A female subject, aged around 80 · a dermatoscopic image of a skin lesion: 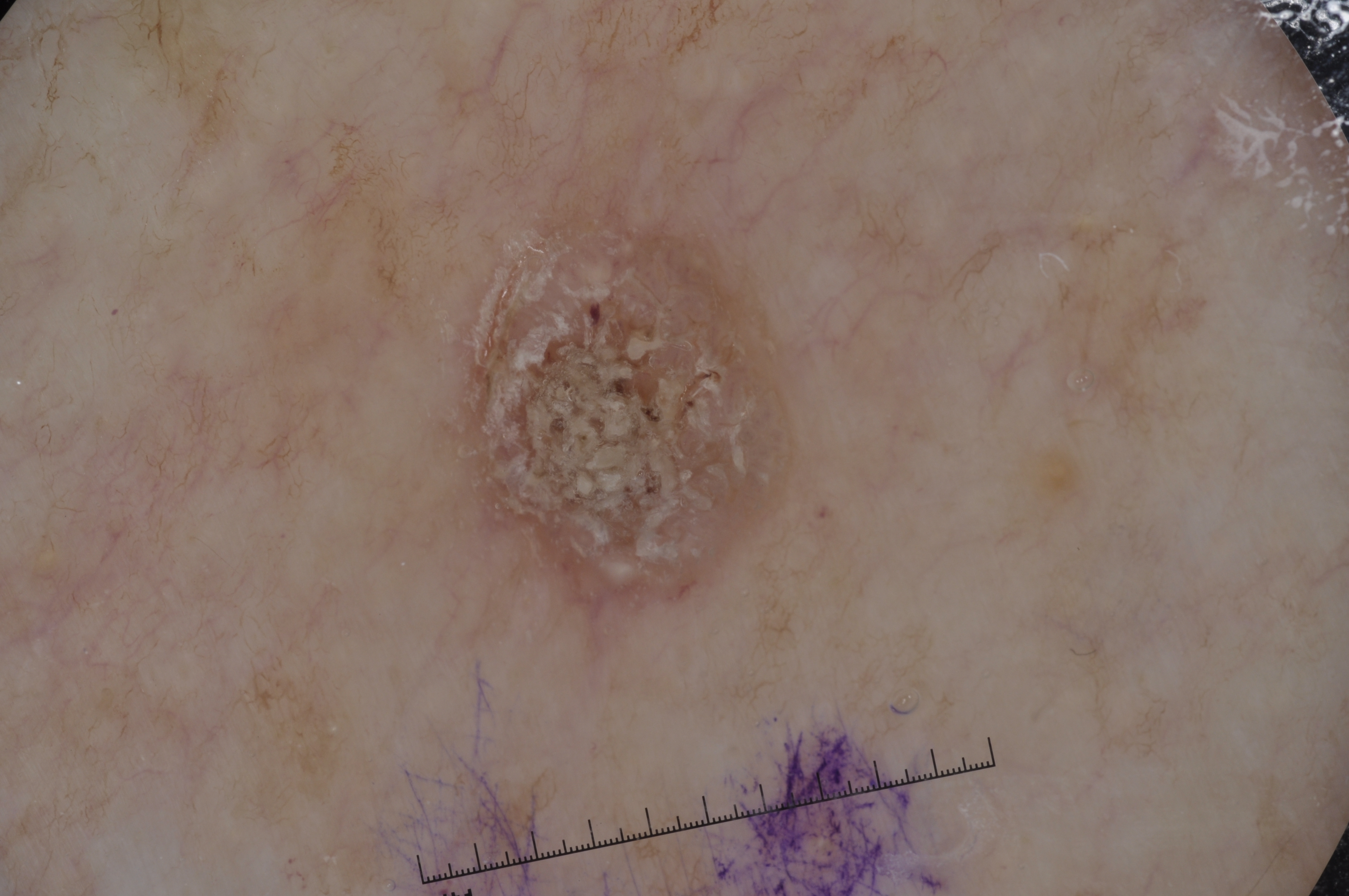  lesion_location:
    bbox_xyxy:
      - 390
      - 168
      - 832
      - 644
  lesion_extent: moderate
  dermoscopic_features:
    present:
      - milia-like cysts
    absent:
      - pigment network
      - negative network
      - streaks
  diagnosis:
    name: seborrheic keratosis
    malignancy: benign
    lineage: keratinocytic
    provenance: clinical